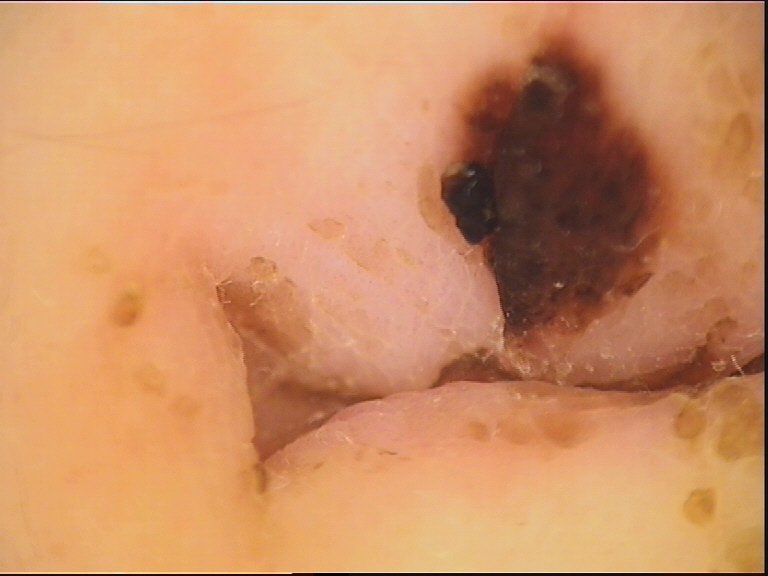modality=dermoscopy
lesion type=keratinocytic
diagnosis=seborrheic keratosis (expert consensus)